A male patient in their mid- to late 30s. Contact-polarized dermoscopy of a skin lesion.
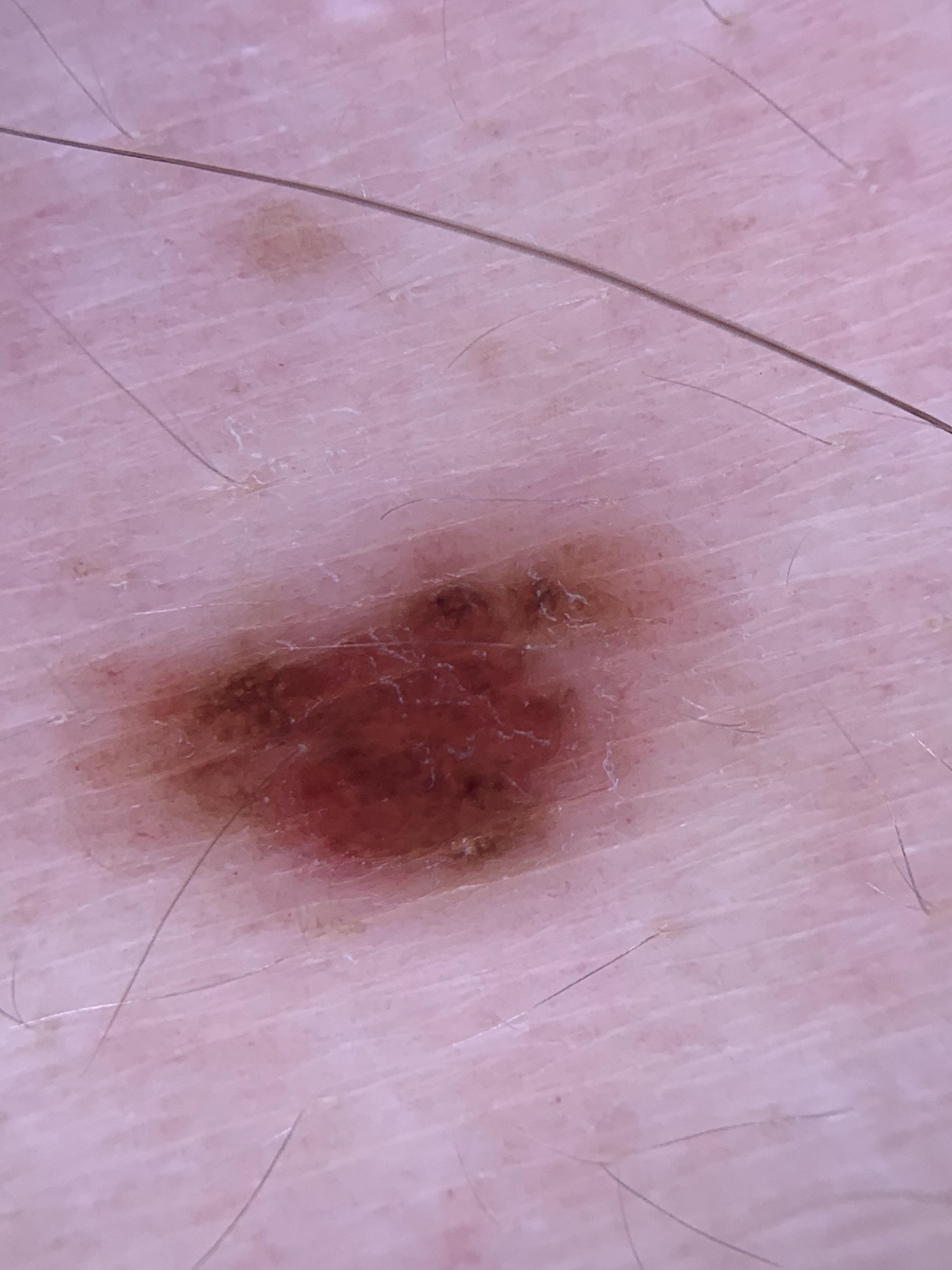The lesion was found on the posterior trunk. Histopathological examination showed a nevus.